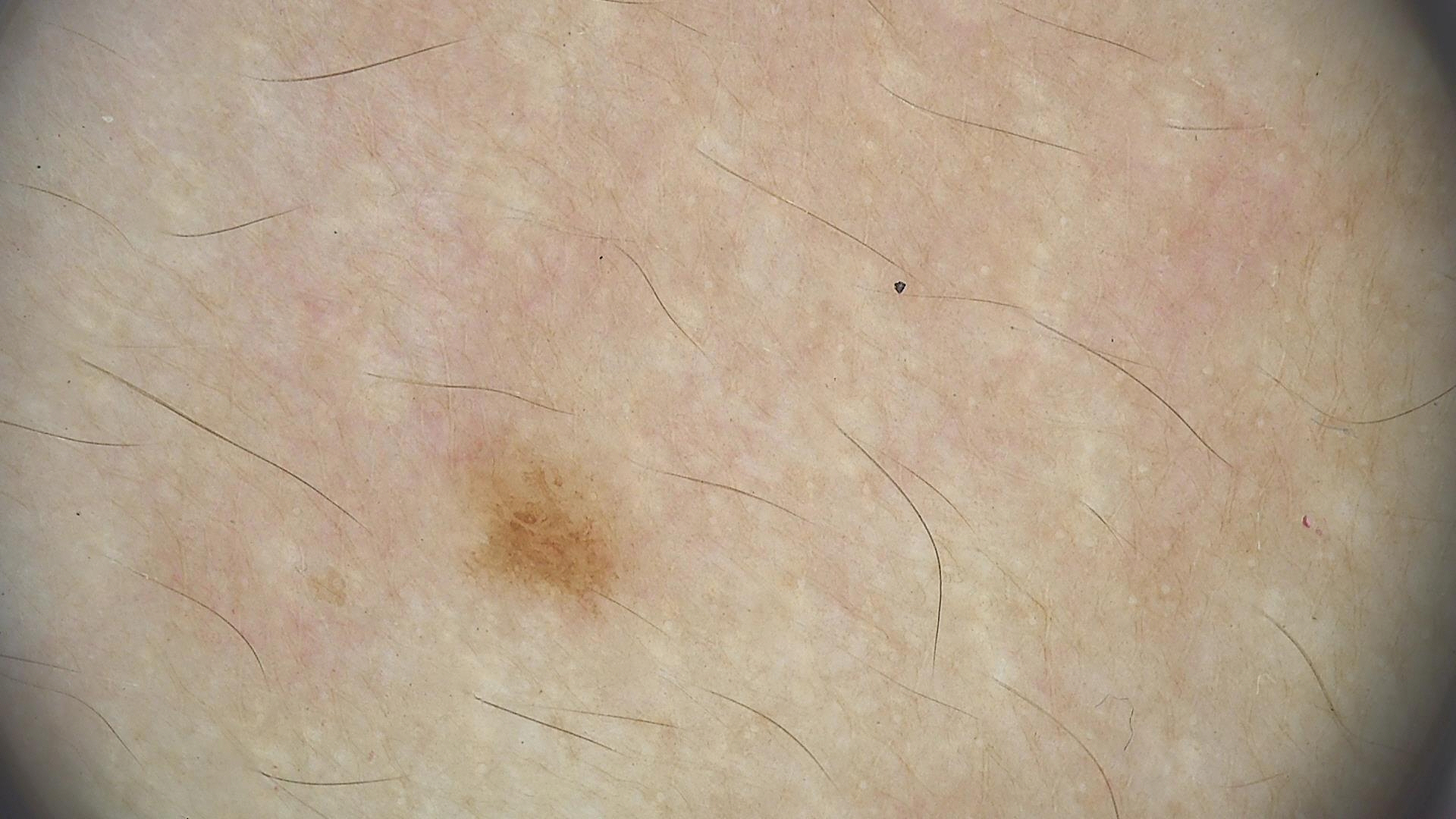diagnosis:
  name: junctional nevus
  code: jb
  malignancy: benign
  super_class: melanocytic
  confirmation: expert consensus